Reported duration is about one day; the affected area is the arm and leg; FST III; this image was taken at a distance; the lesion is described as raised or bumpy; the patient considered this a rash; the lesion is associated with burning, itching and bothersome appearance: 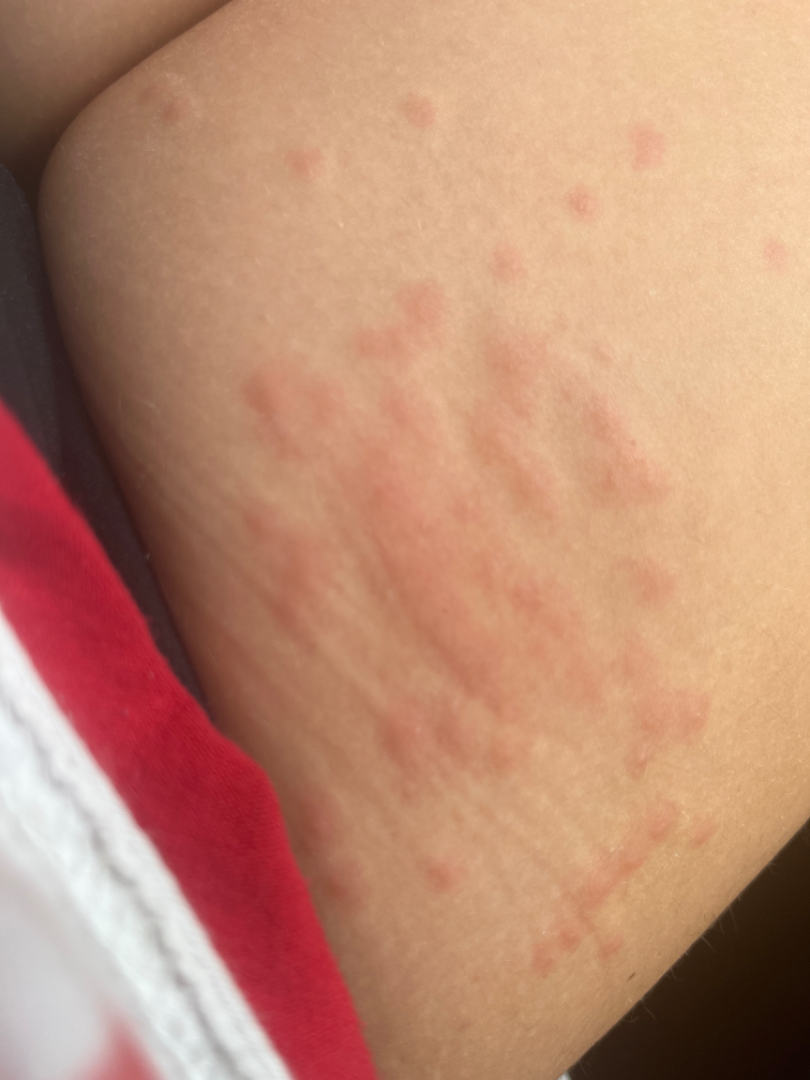assessment = unable to determine.